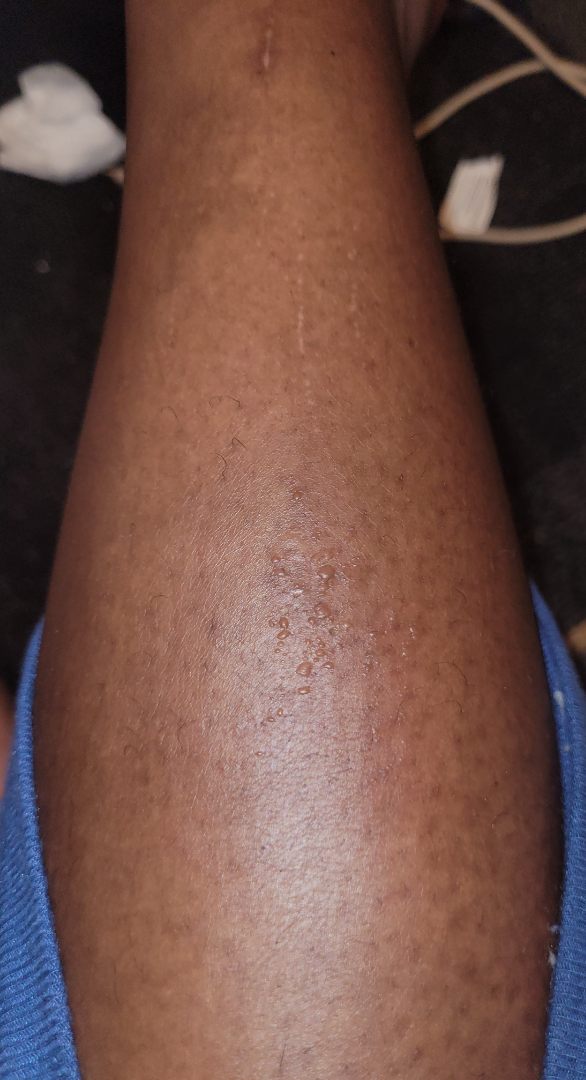Diagnostic features were not clearly distinguishable in this photograph. The contributor reports the condition has been present for less than one week. No associated systemic symptoms reported. The leg is involved. The patient considered this skin that appeared healthy to them. Close-up view. Reported lesion symptoms include itching. The lesion is described as raised or bumpy.